Self-categorized by the patient as skin that appeared healthy to them · the affected area is the leg and arm · the photograph is a close-up of the affected area.
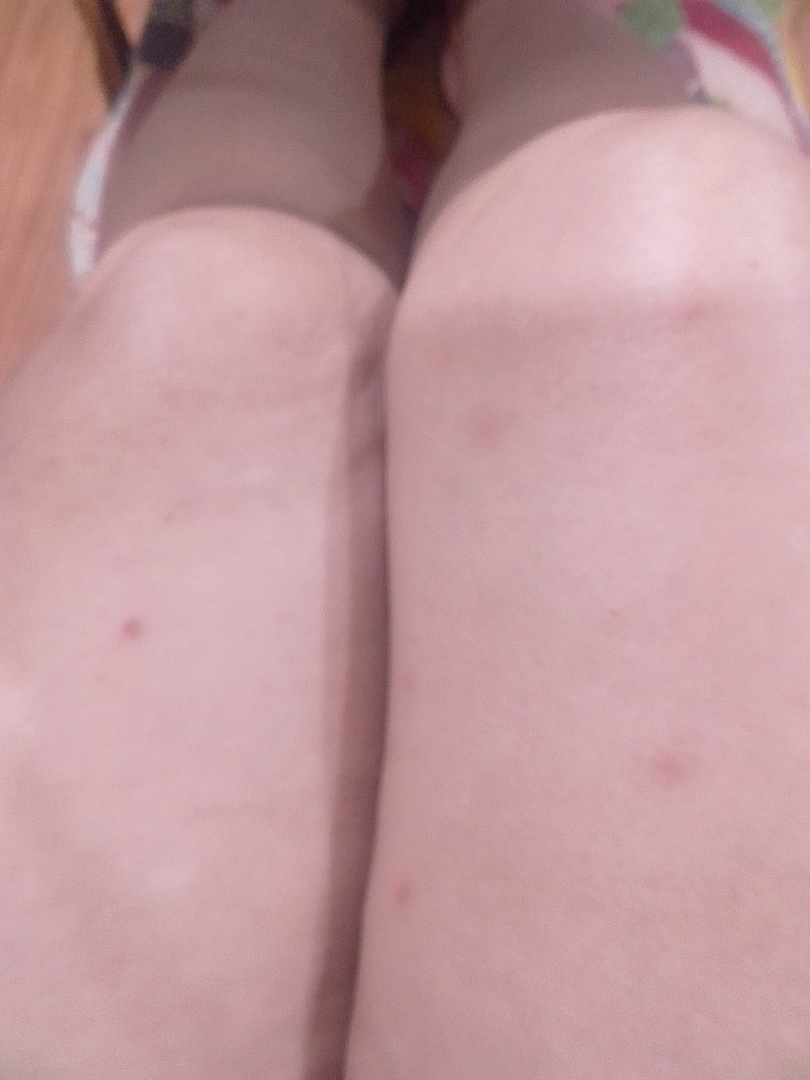{
  "assessment": "indeterminate"
}